A dermoscopic photograph of a skin lesion.
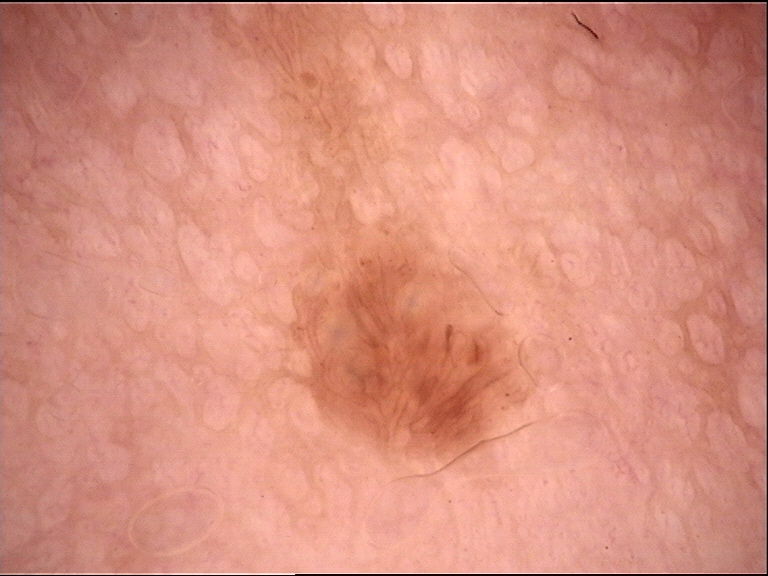This is a banal lesion.
Consistent with a dermal nevus.